A dermoscopic photograph of a skin lesion.
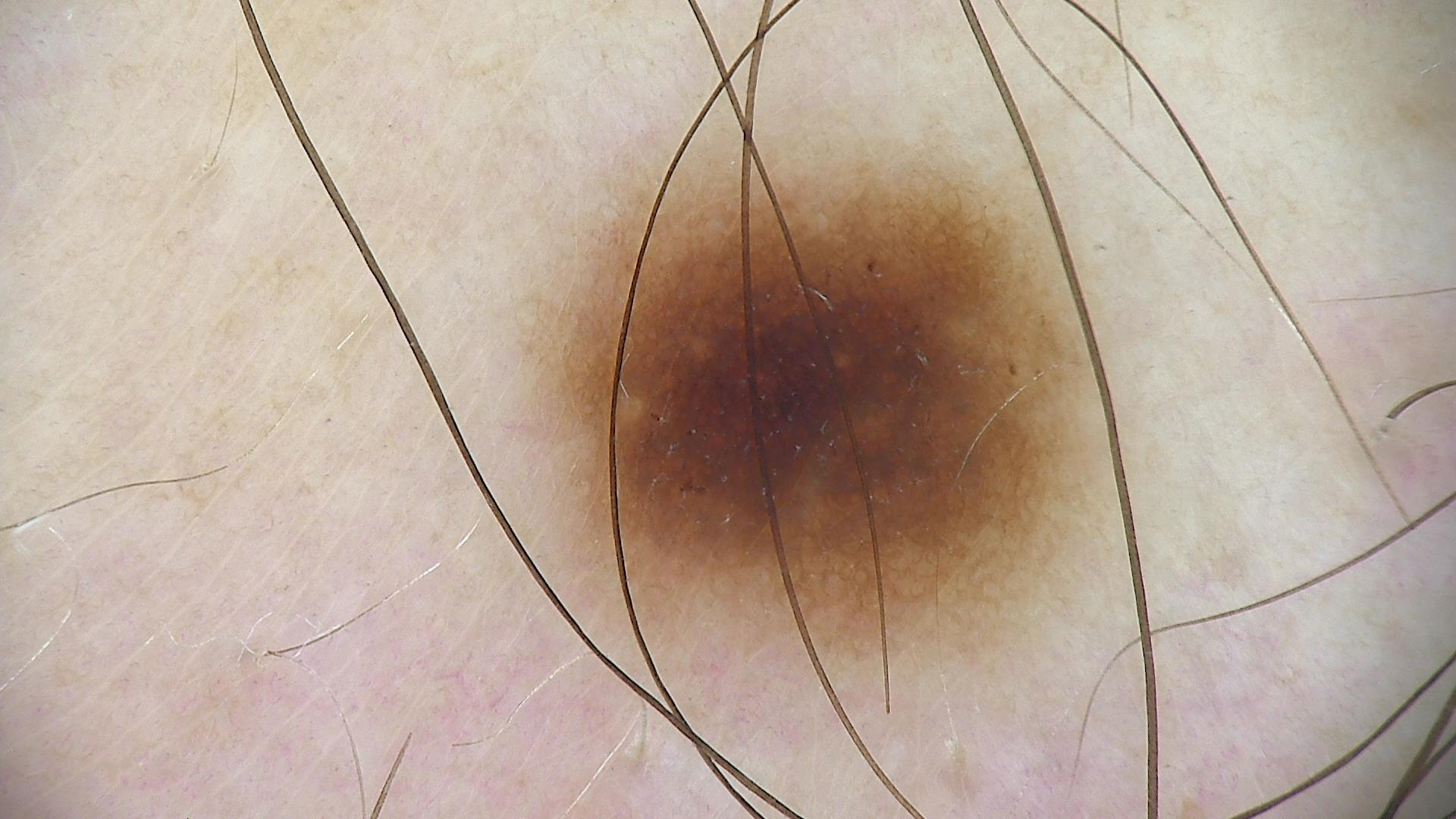Impression:
Consistent with a benign lesion — a dysplastic junctional nevus.